The patient considered this a rash · the photograph was taken at an angle · the contributor notes the lesion is raised or bumpy · the affected area is the leg · lay reviewers estimated Monk Skin Tone 2 (US pool) or 1 (India pool) · the condition has been present for one to four weeks: 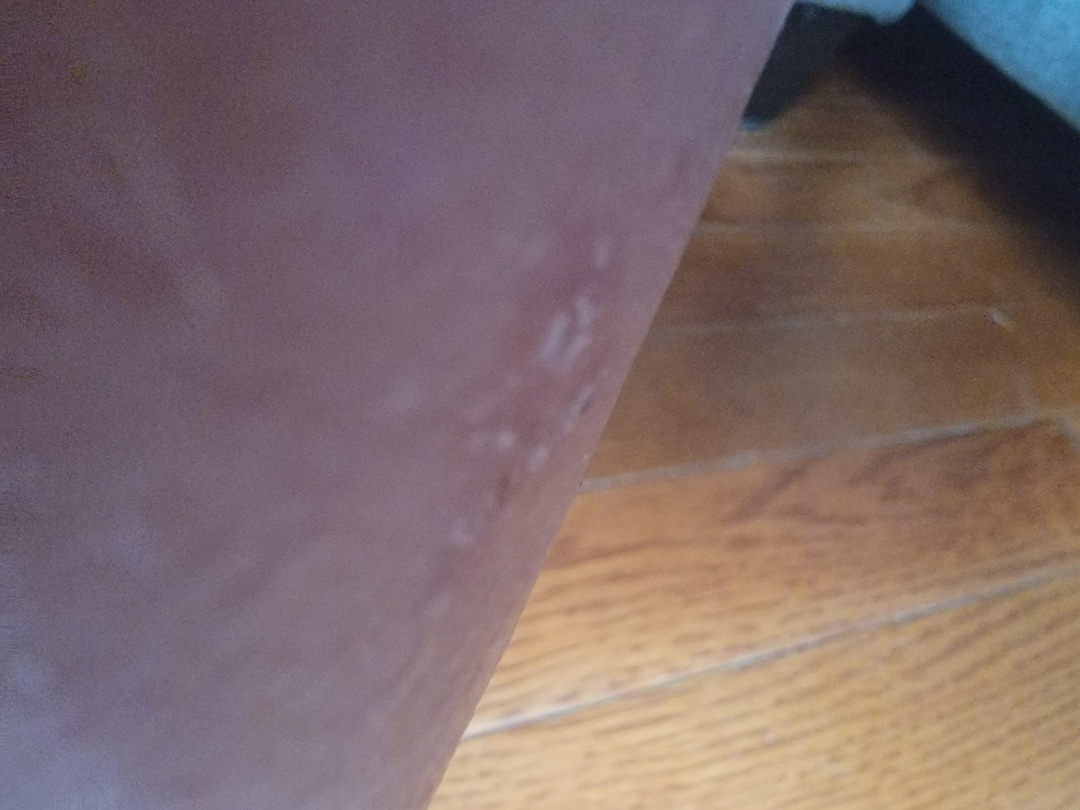Assessment:
On remote review of the image, Acute and chronic dermatitis (considered); Irritant Contact Dermatitis (considered).